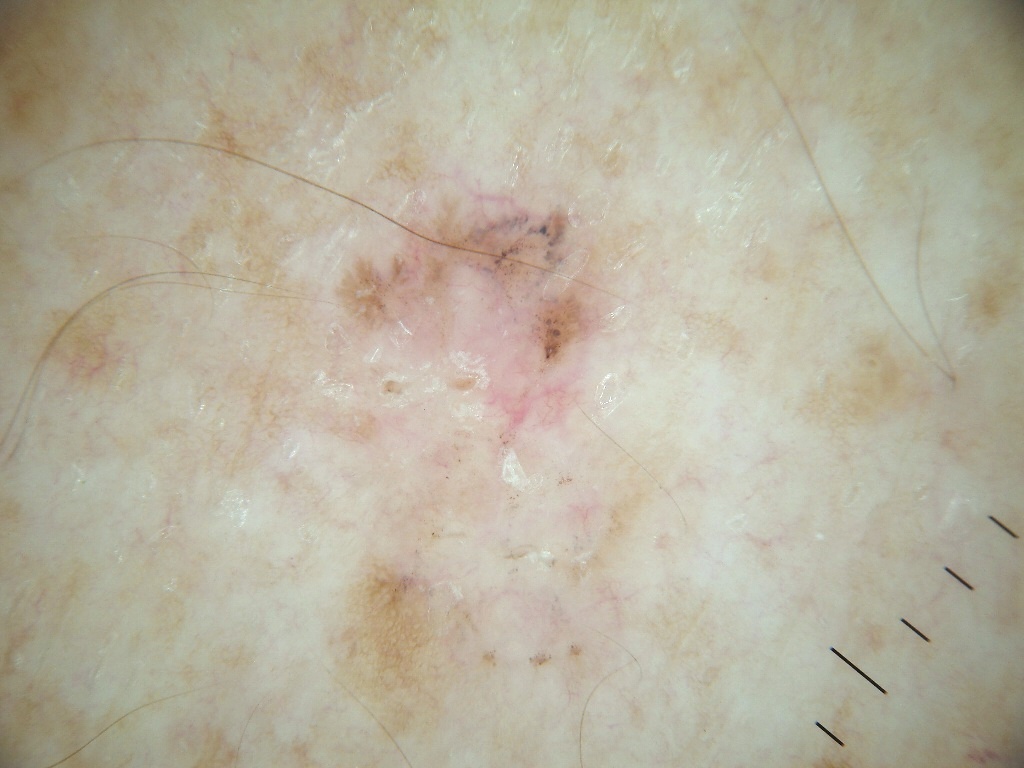modality = dermoscopy | size = moderate | absent dermoscopic findings = globules and streaks | lesion bbox = (295, 171, 641, 639) | impression = a malignancy.